The affected area is the head or neck and arm. The photograph was taken at a distance.
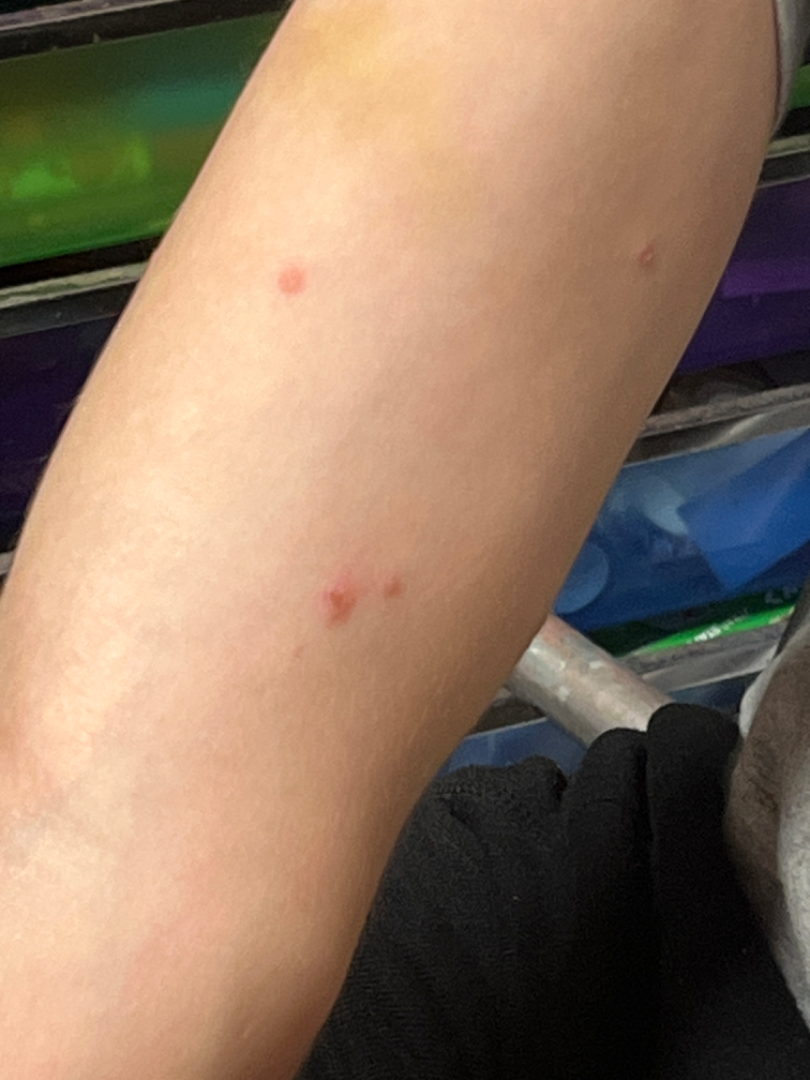differential: the impression on review was Psoriasis